A dermatoscopic image of a skin lesion.
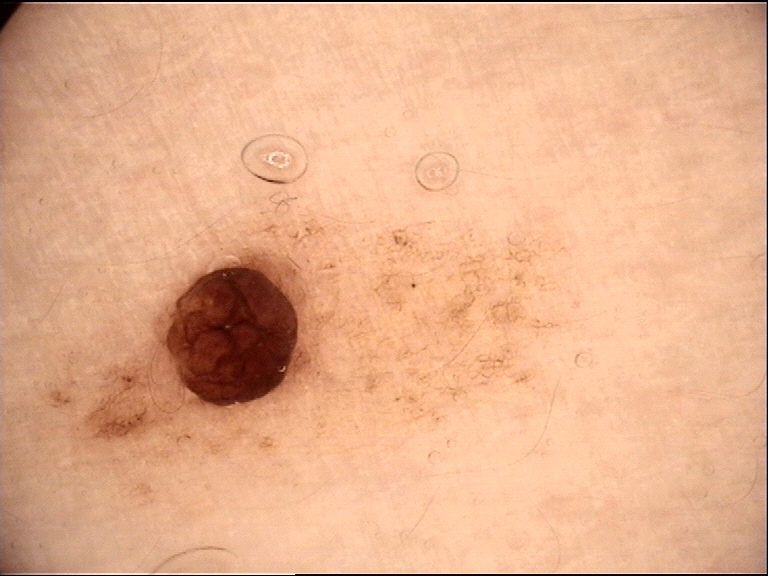{
  "lesion_type": {
    "main_class": "banal",
    "pattern": "dermal"
  },
  "diagnosis": {
    "name": "dermal nevus",
    "code": "db",
    "malignancy": "benign",
    "super_class": "melanocytic",
    "confirmation": "expert consensus"
  }
}